Close-up view; located on the leg:
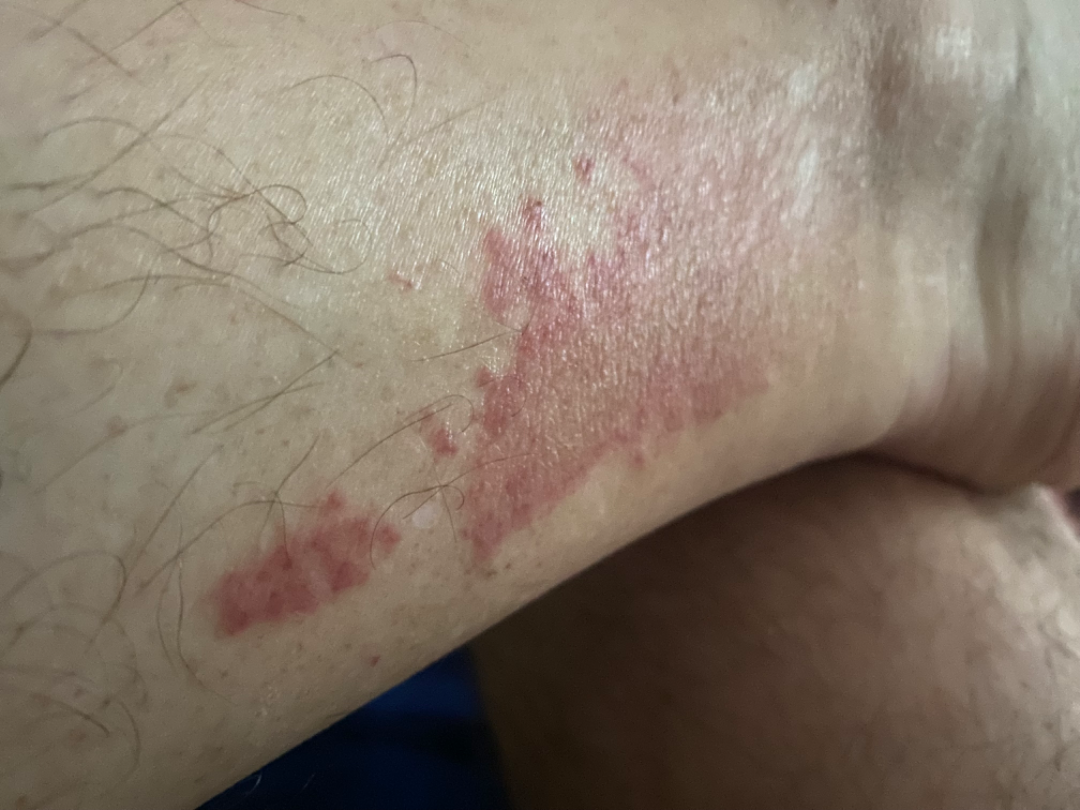| feature | finding |
|---|---|
| assessment | one reviewing dermatologist: the leading consideration is Tinea; the differential also includes Psoriasis; an alternative is Eczema |